Texture is reported as raised or bumpy. Associated systemic symptoms include mouth sores. The condition has been present for more than one year. The patient is a female aged 18–29. Close-up view:
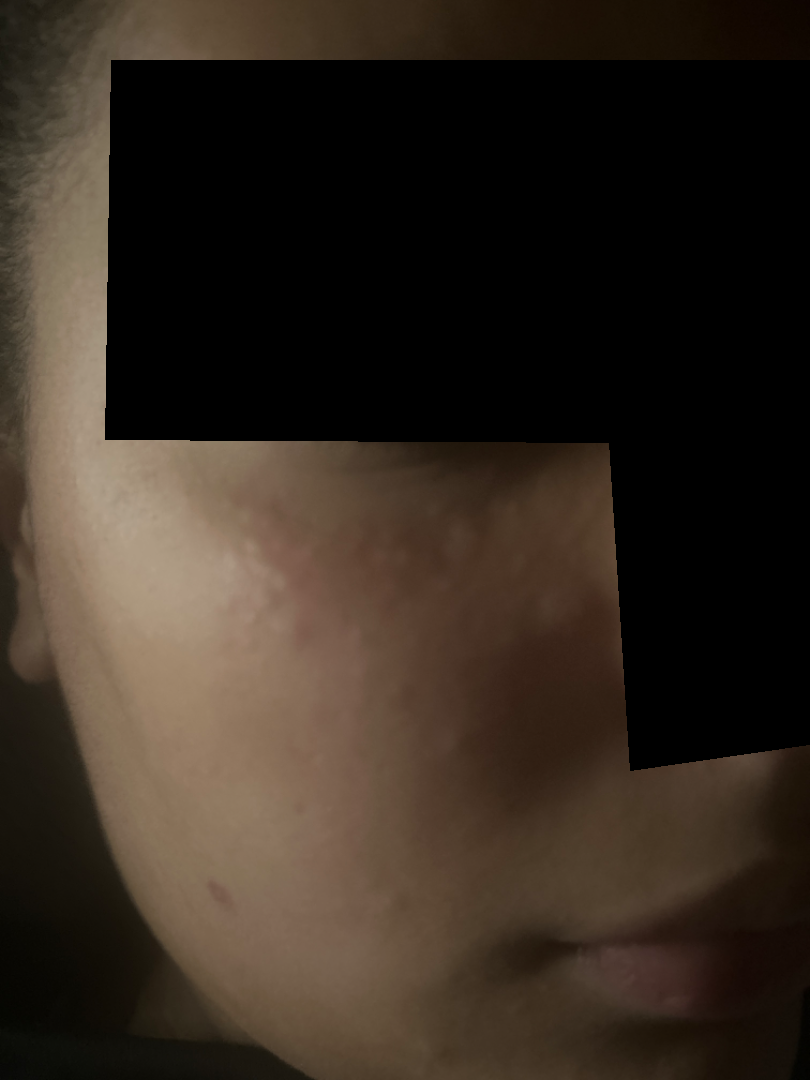<dermatology_case>
  <assessment>could not be assessed</assessment>
</dermatology_case>